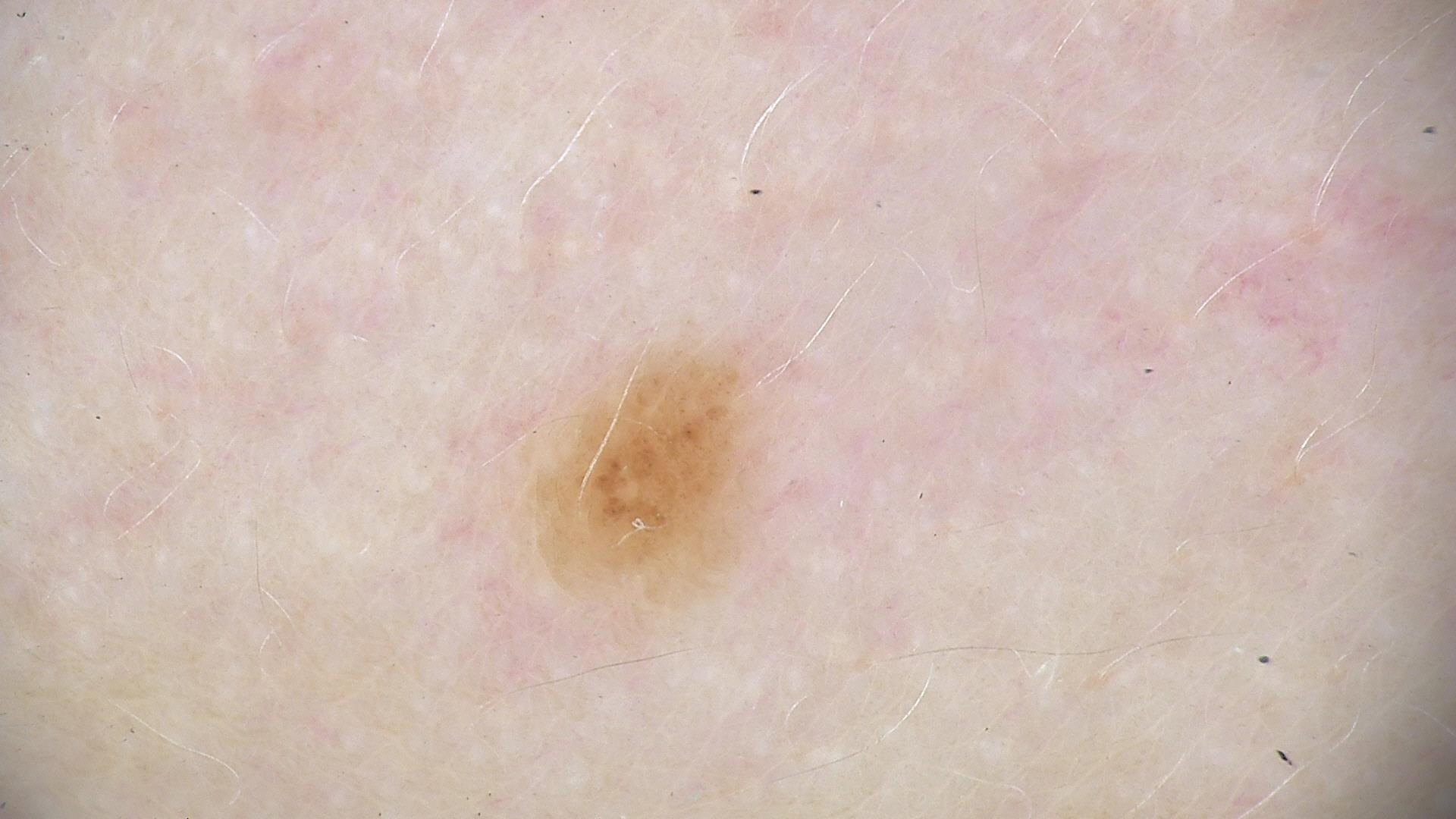Impression:
The diagnosis was a dysplastic junctional nevus.